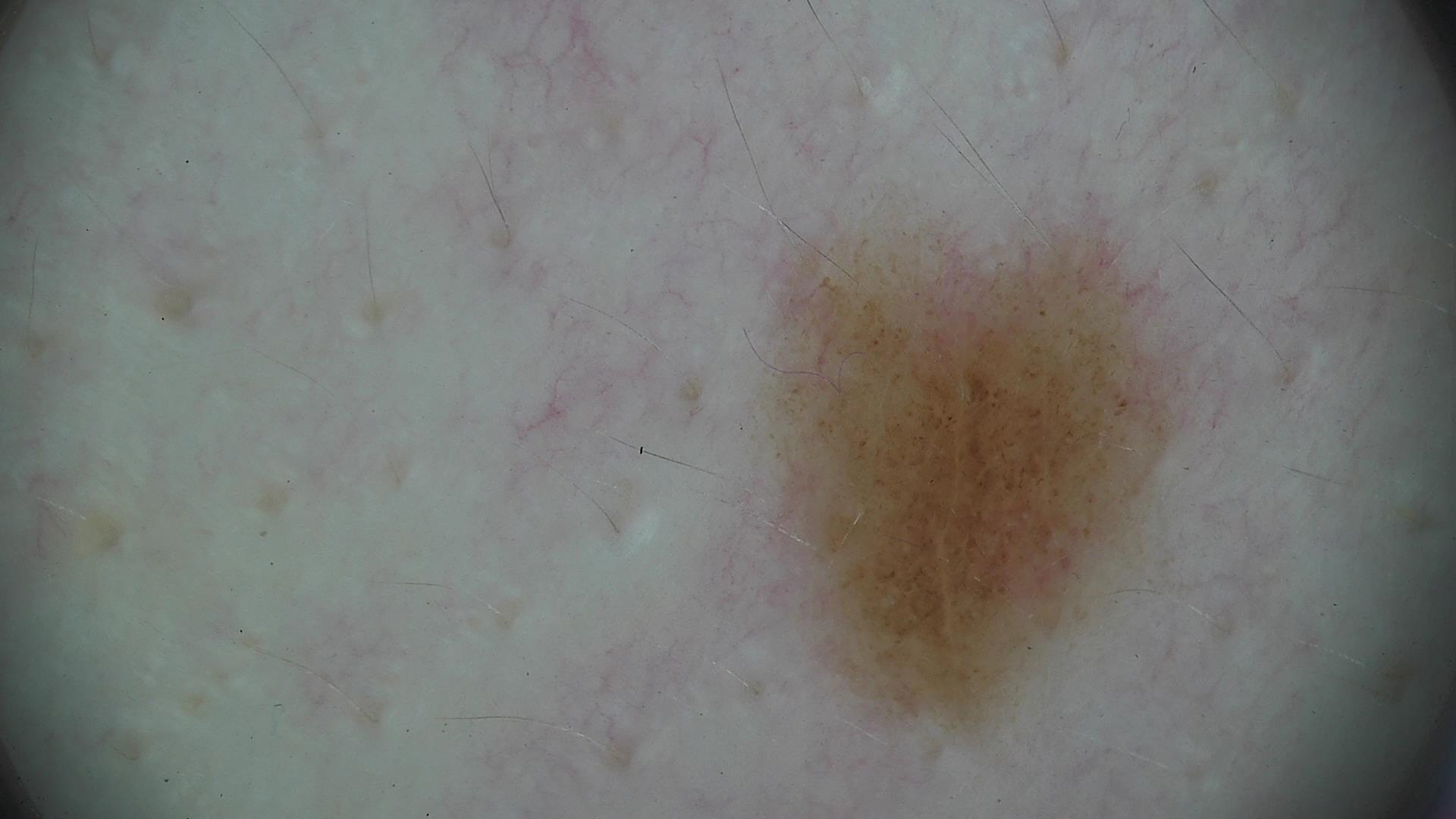A dermoscopy image of a single skin lesion. Consistent with a dysplastic junctional nevus.